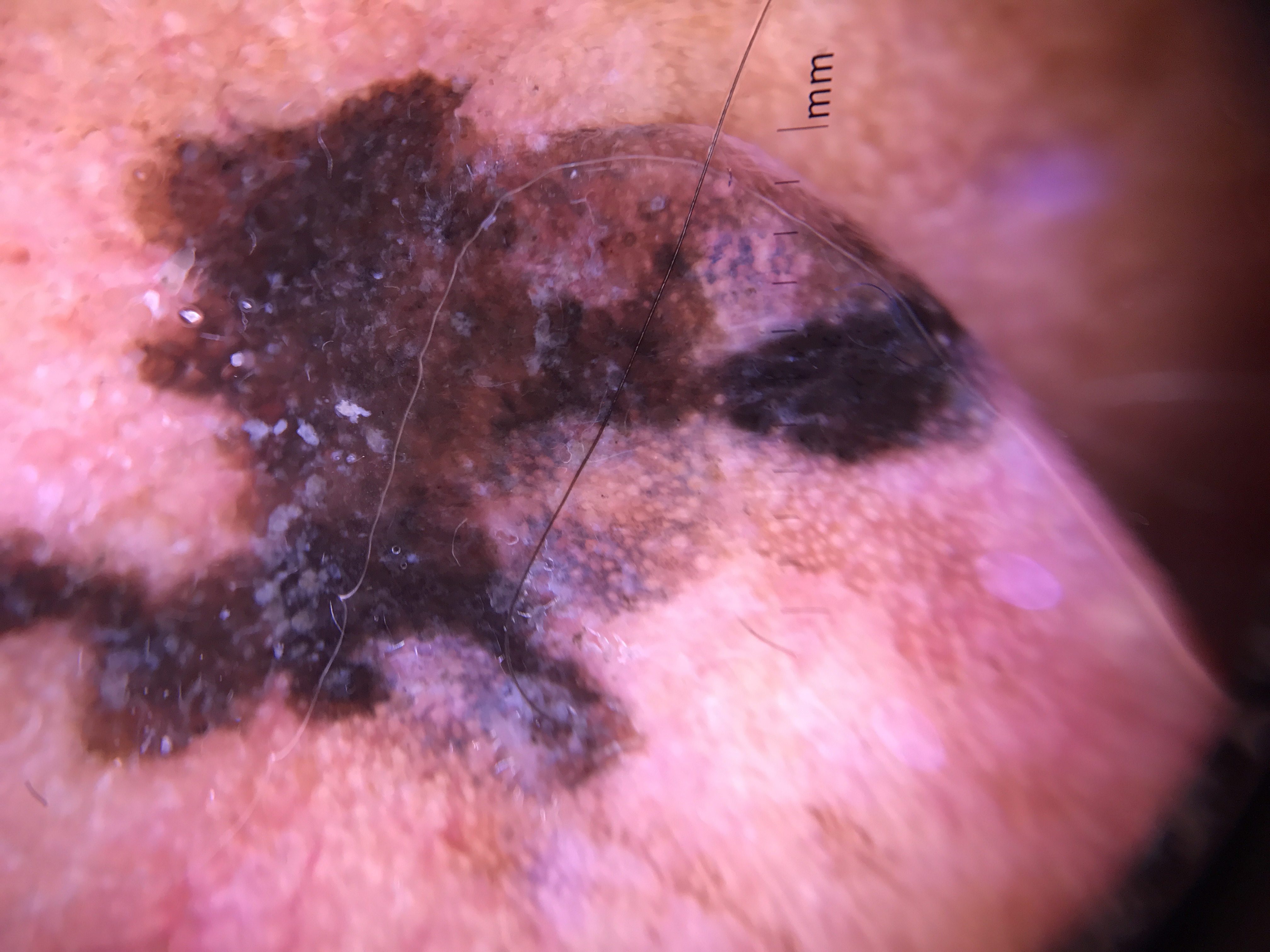Histopathology confirmed a lentigo maligna.